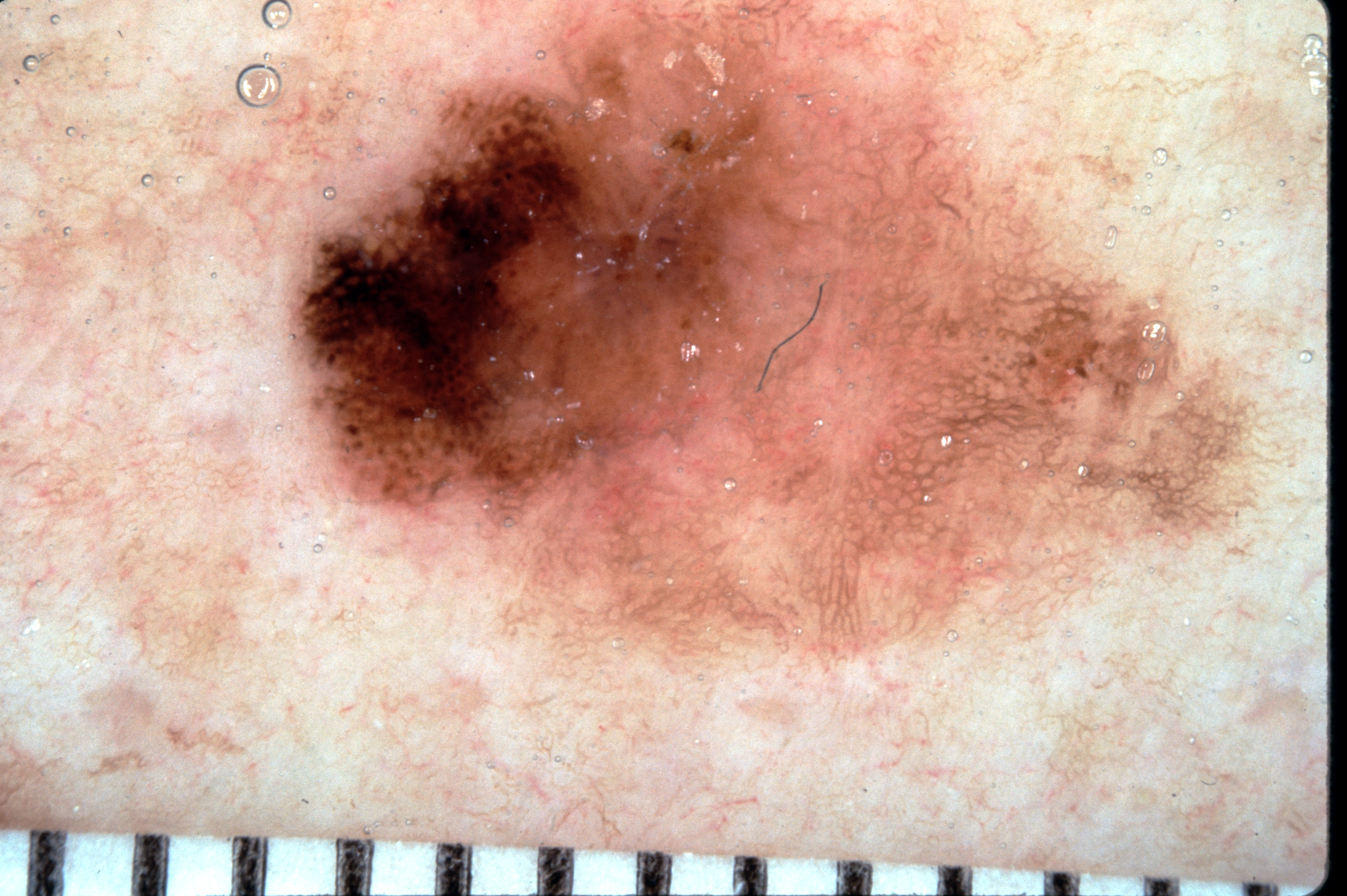Case summary: A dermoscopic view of a skin lesion. The subject is female. With coordinates (x1, y1, x2, y2), the lesion occupies the region (295, 0, 1252, 672). Part of the lesion extends beyond the imaged area. A large lesion occupying much of the field. Dermoscopic assessment notes pigment network; no negative network, milia-like cysts, or streaks. Diagnosis: Biopsy-confirmed as a melanoma, a skin cancer.